A dermatoscopic image of a skin lesion:
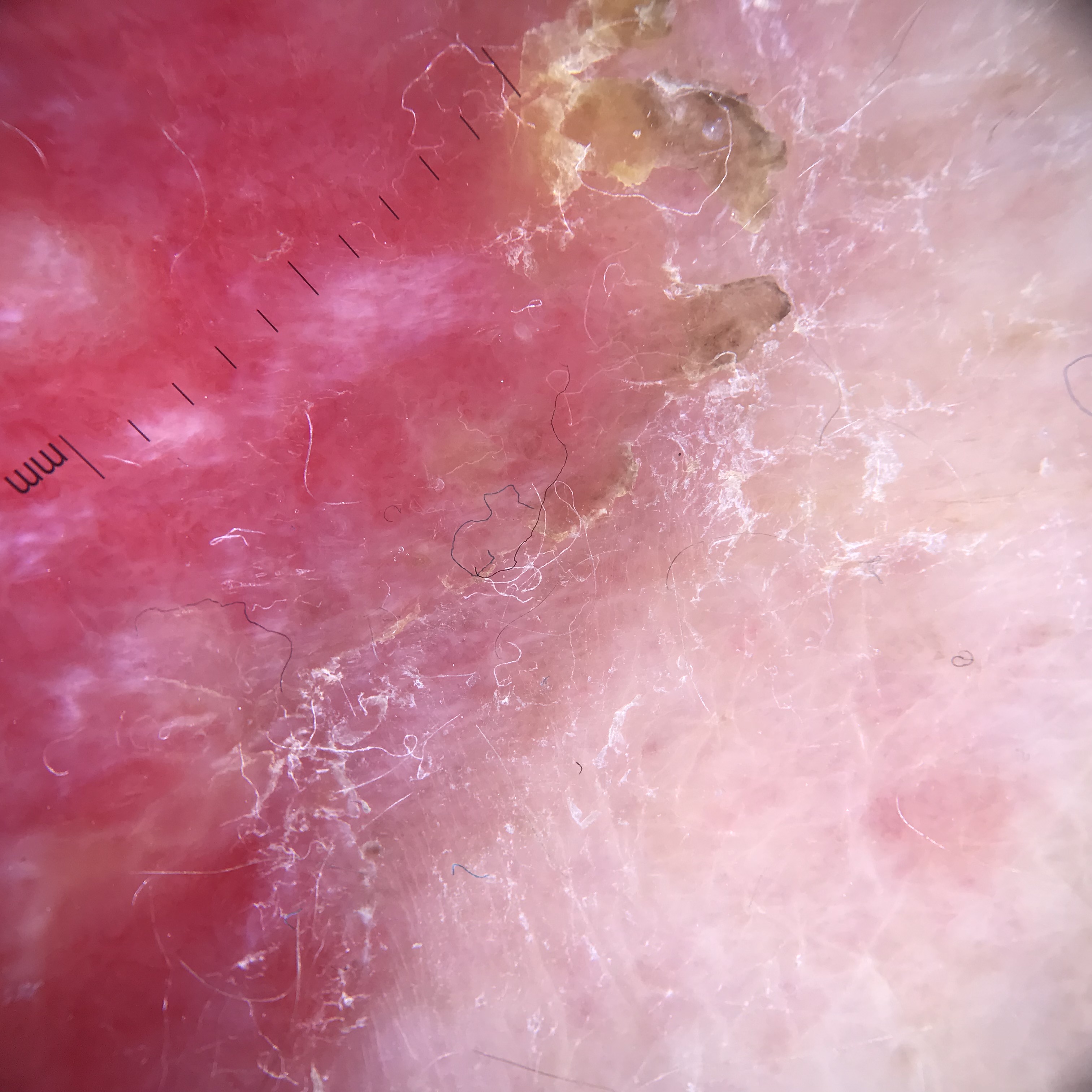diagnostic label=Bowen's disease (biopsy-proven)